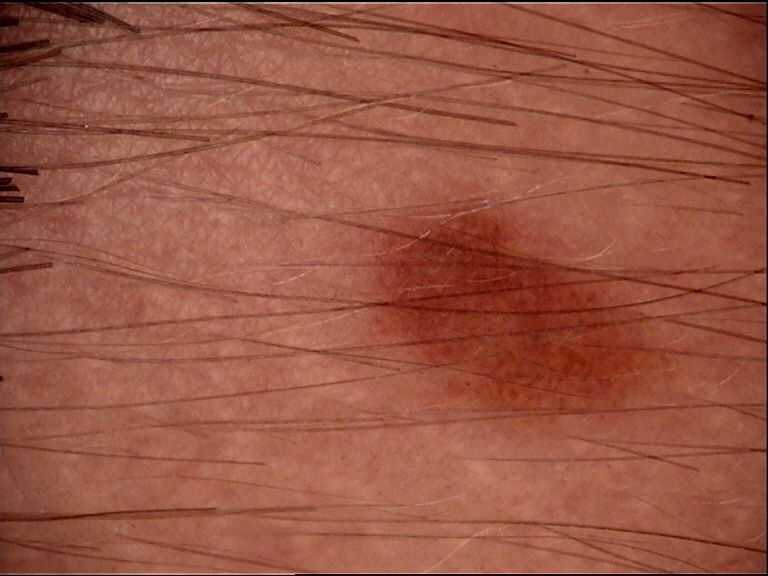A dermoscopy image of a single skin lesion.
This is a banal lesion.
Diagnosed as a junctional nevus.